Dermoscopy of a skin lesion.
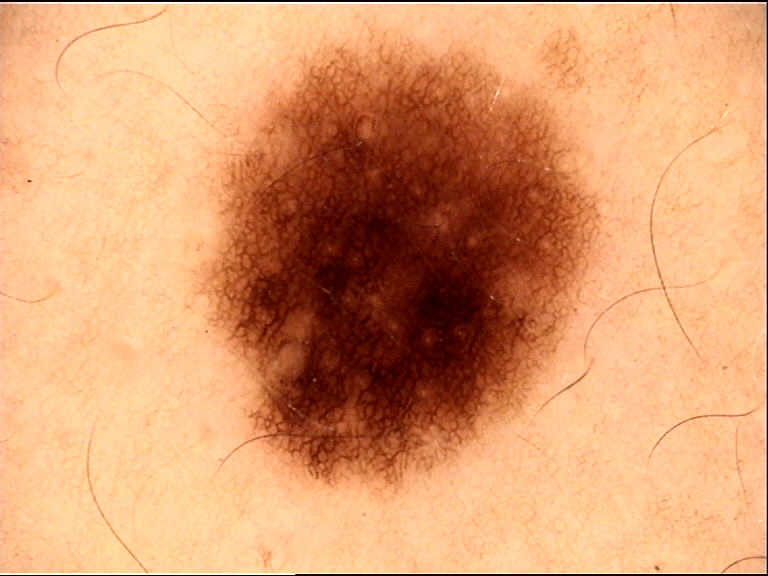Q: What is this lesion?
A: dysplastic junctional nevus (expert consensus)